Dermoscopy of a skin lesion.
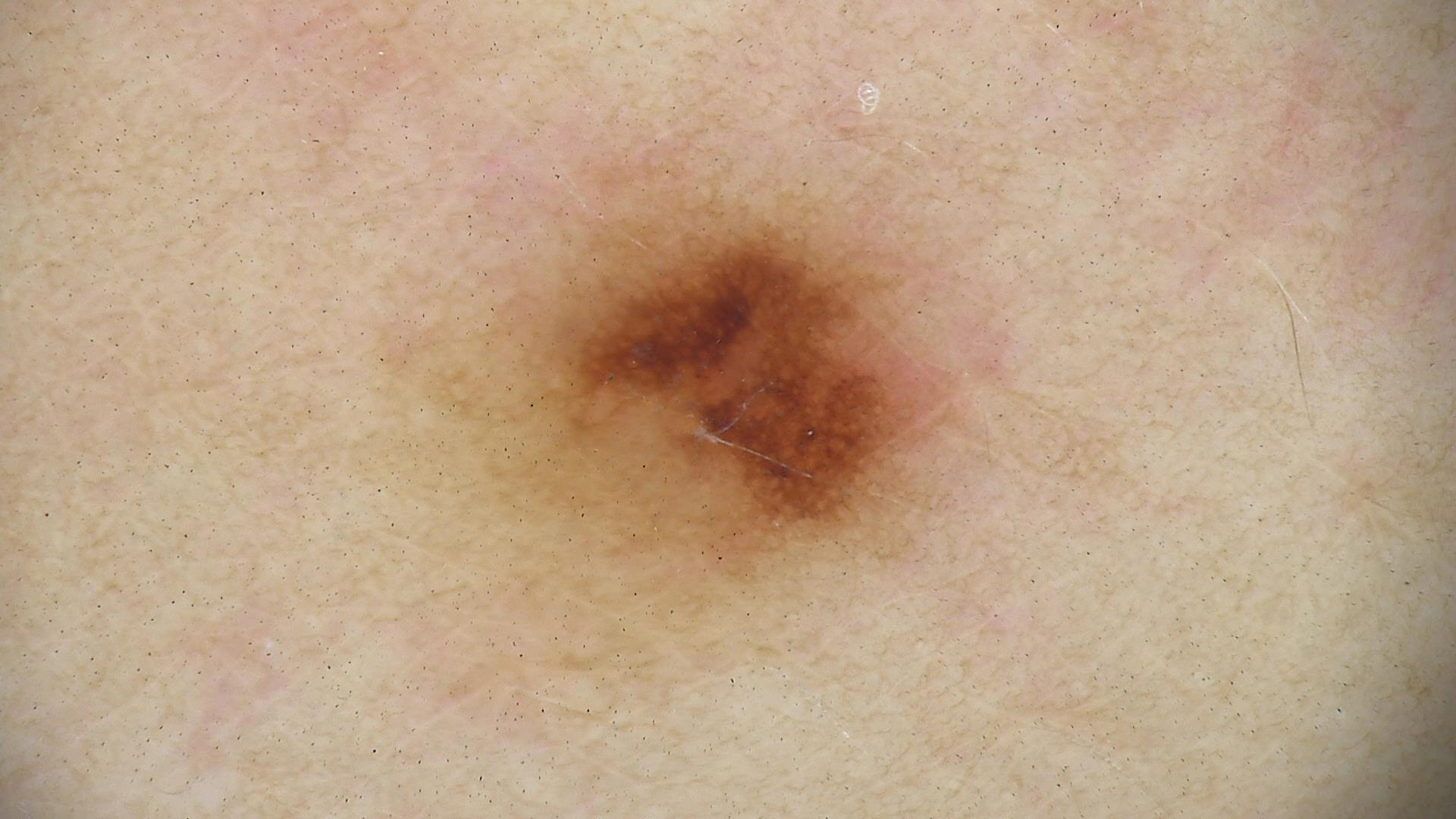Conclusion: Consistent with a dysplastic junctional nevus.